The affected area is the arm, back of the torso, back of the hand and front of the torso; close-up view; female contributor, age 50–59 — 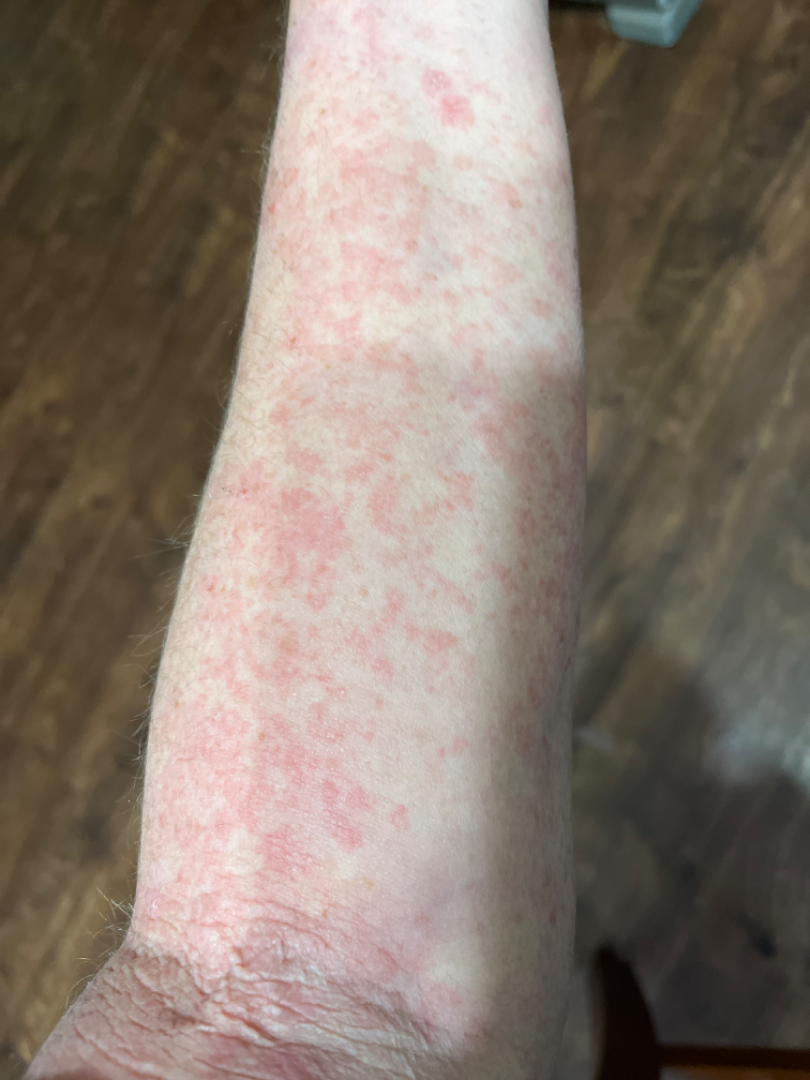{"systemic_symptoms": ["fatigue", "joint pain"], "patient_category": "a rash", "texture": ["flat", "raised or bumpy"], "differential": {"tied_lead": ["Drug Rash", "Urticaria"]}}